A close-up photograph:
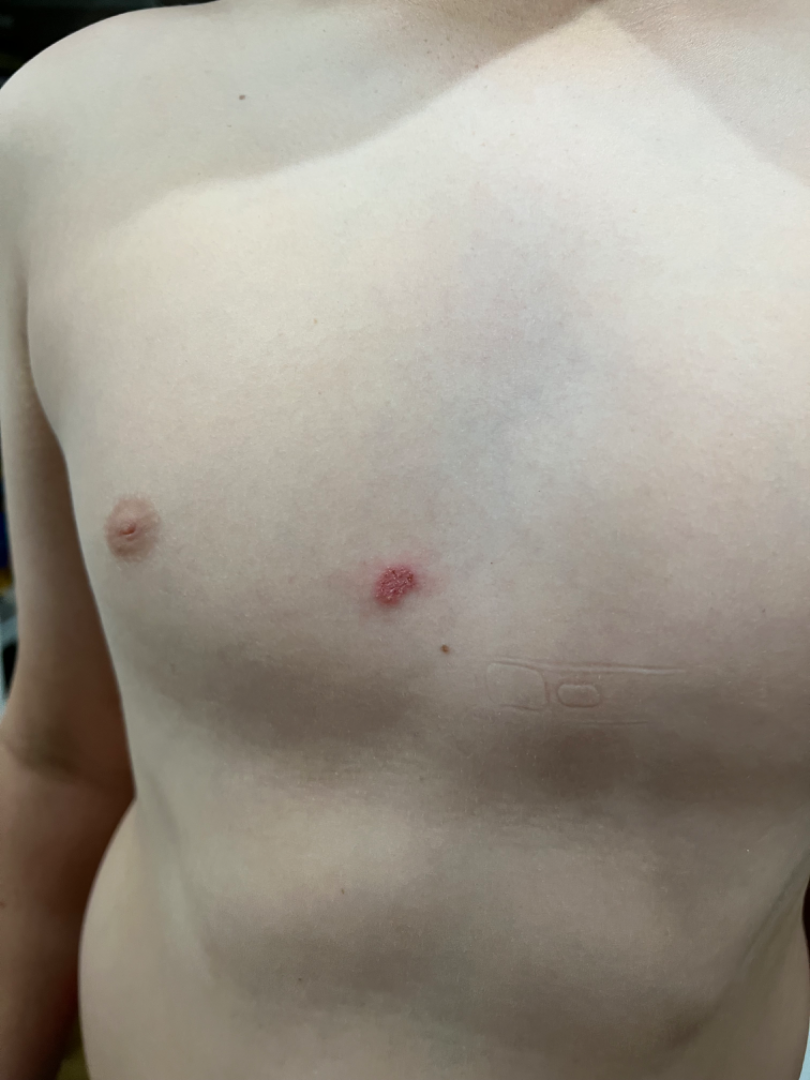The skin condition could not be confidently assessed from this image.
Self-categorized by the patient as a rash.
Present for about one day.
Reported lesion symptoms include itching.